A dermoscopic close-up of a skin lesion.
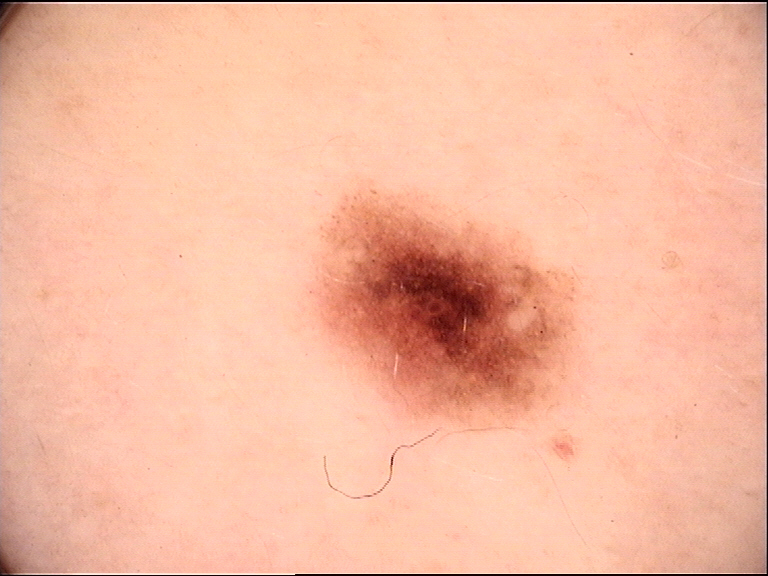{"diagnosis": {"name": "dysplastic junctional nevus", "code": "jd", "malignancy": "benign", "super_class": "melanocytic", "confirmation": "expert consensus"}}